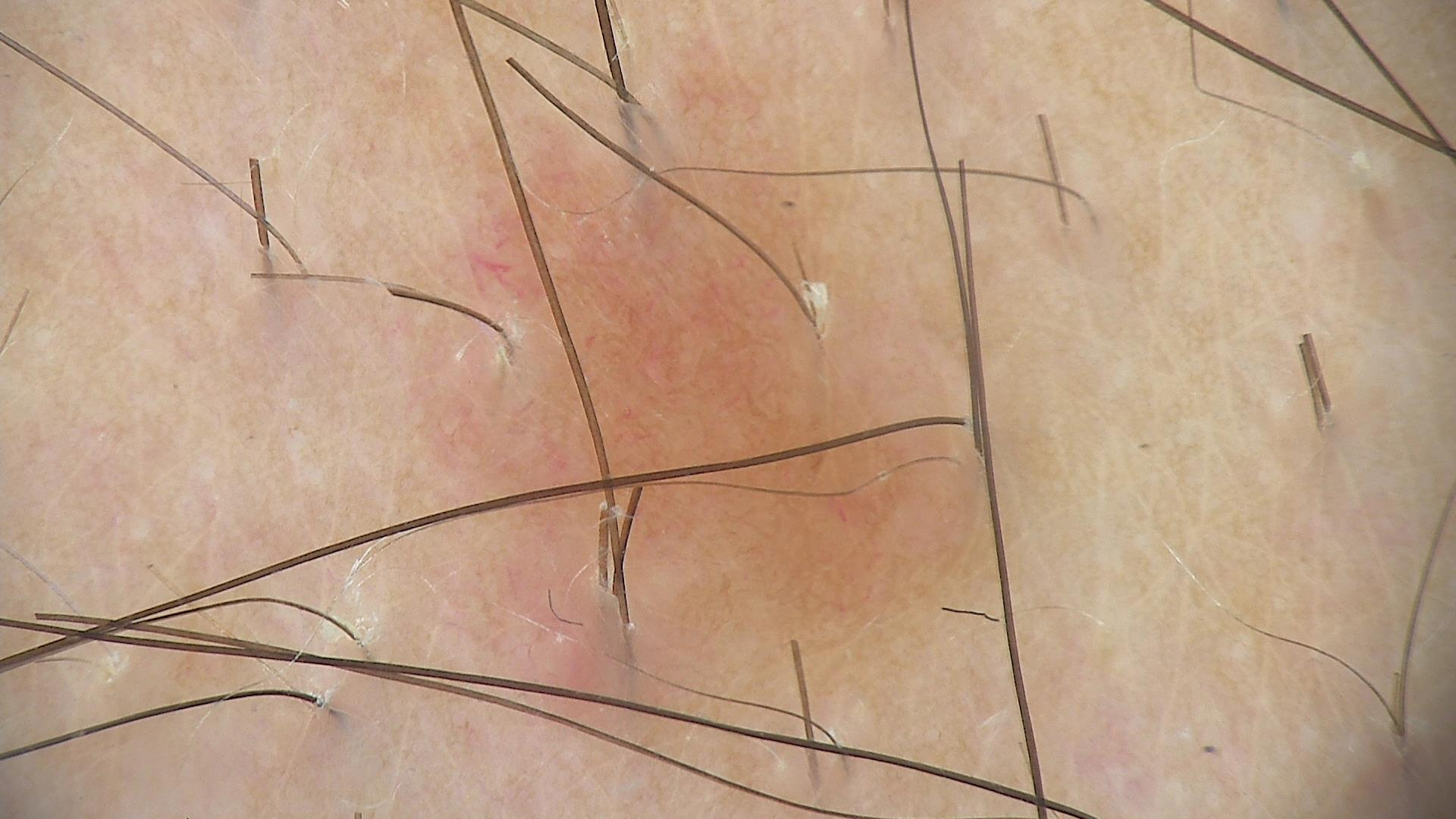Case:
* class — dermal nevus (expert consensus)